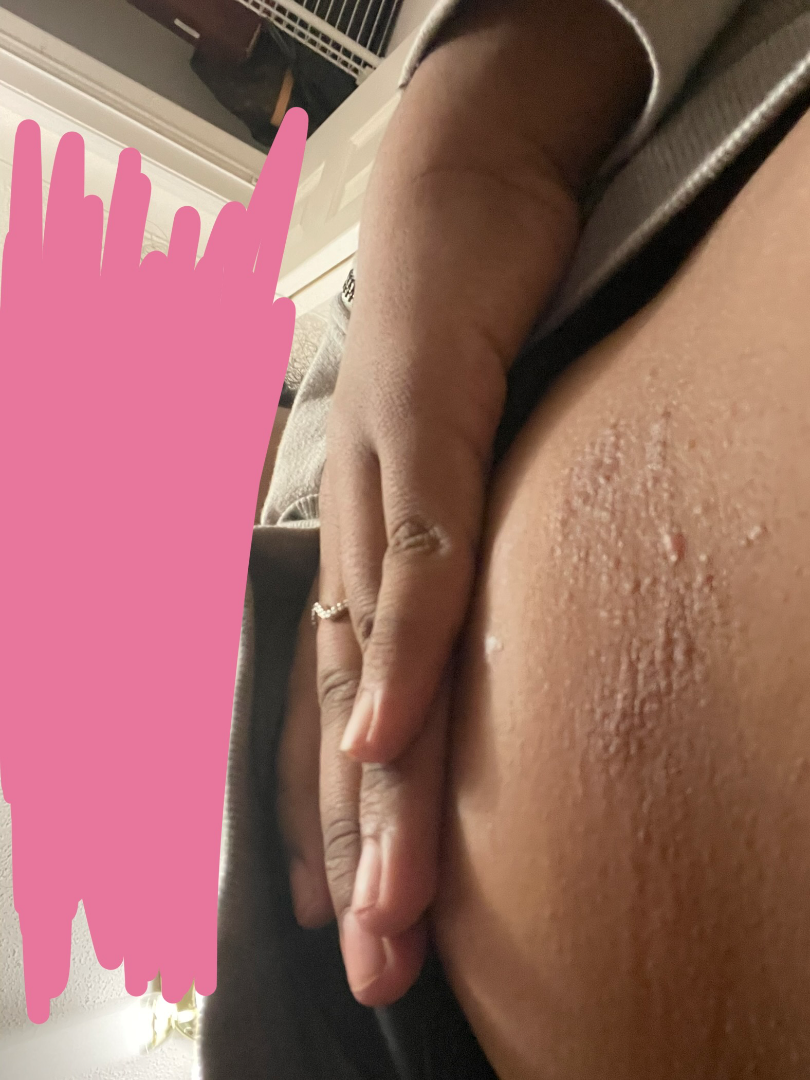differential=the leading consideration is Allergic Contact Dermatitis; an alternative is Eczema